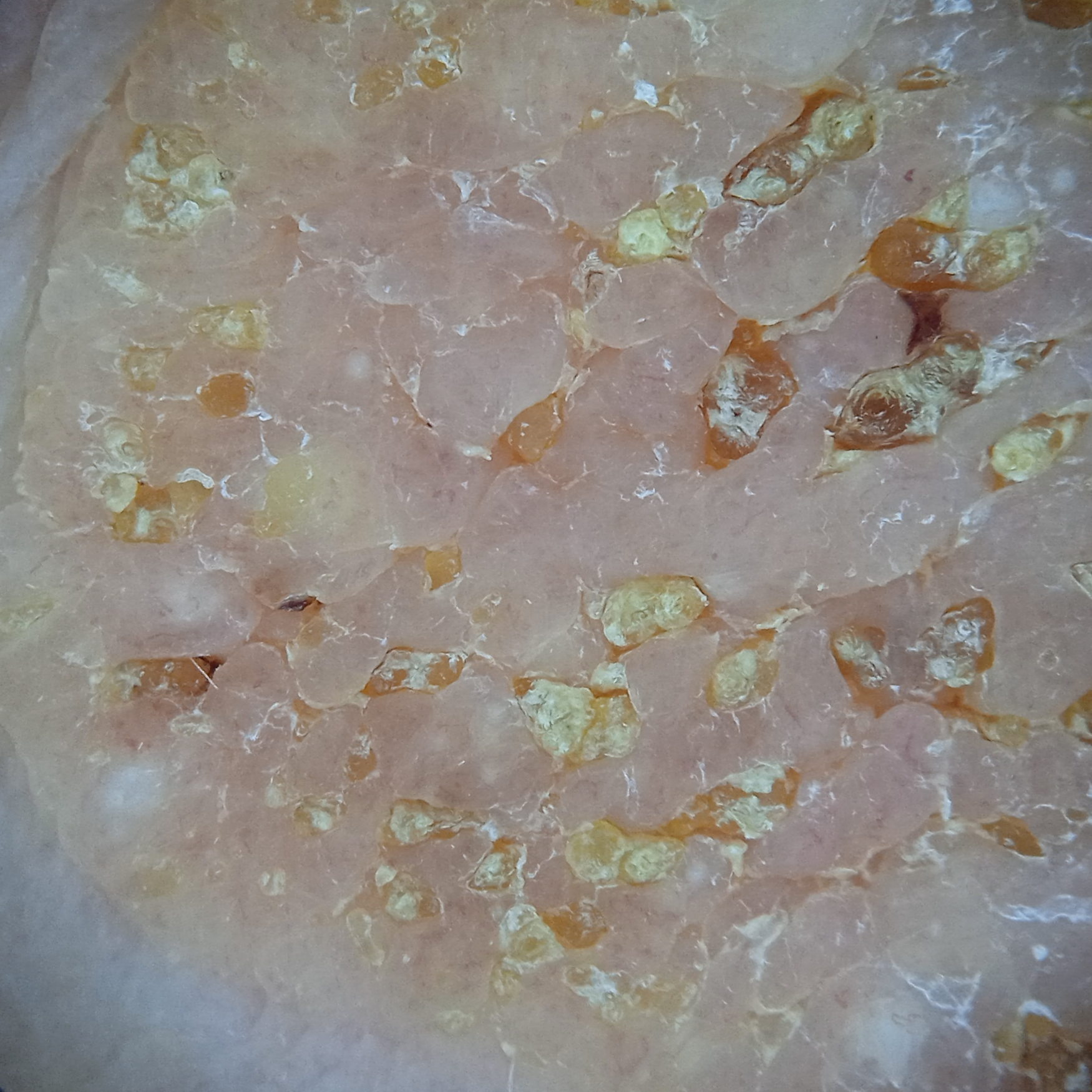By self-report, no personal history of cancer.
A dermatoscopic image of a skin lesion.
Collected as part of a research study, without a referral diagnosis.
A female subject 81 years of age.
A moderate number of moles by the patient's own estimate.
The patient says their skin reddens painfully with sun exposure.
The lesion involves the torso.
The diagnostic impression was a seborrheic keratosis.